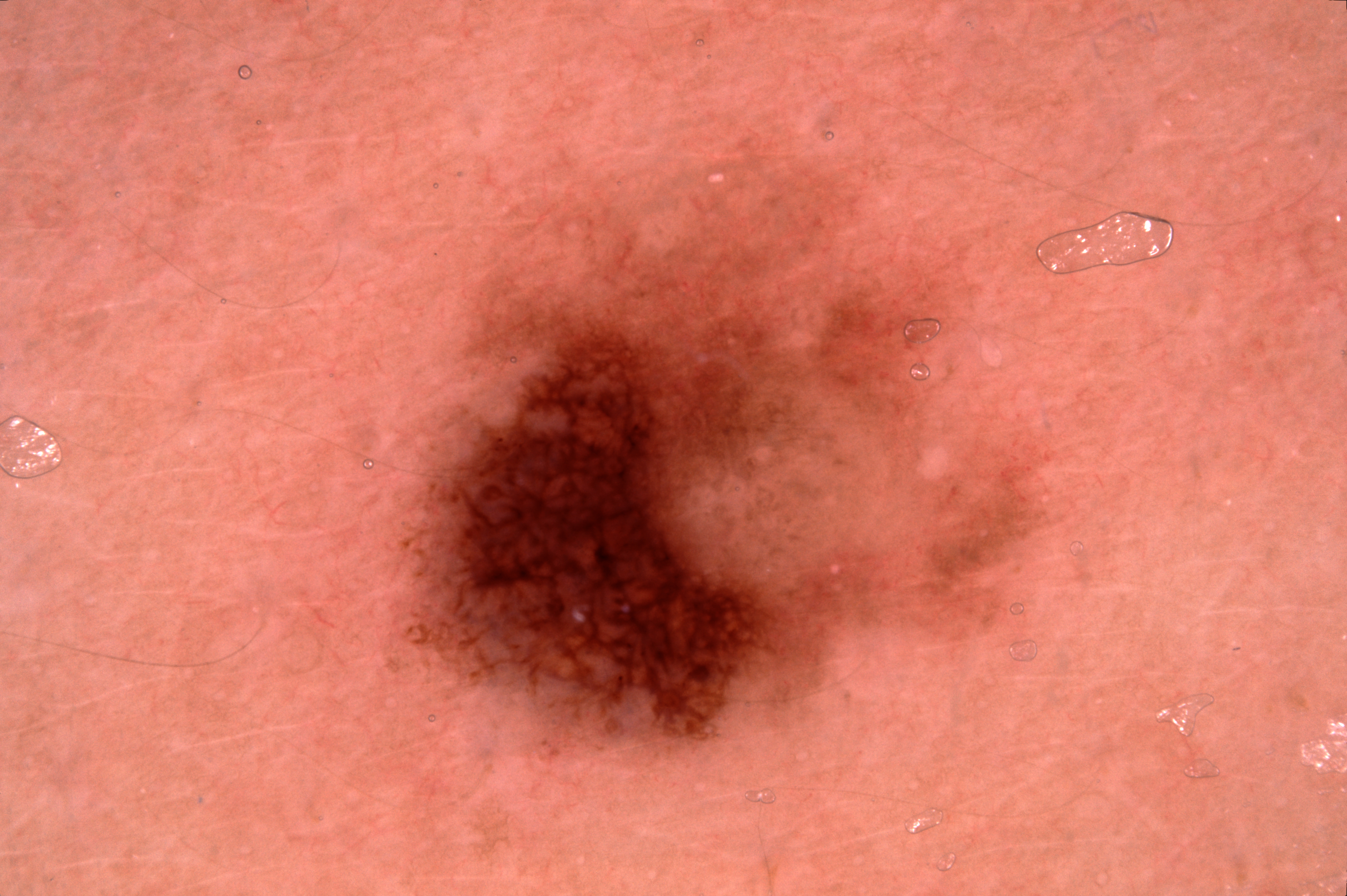Q: What is the imaging modality?
A: dermoscopy
Q: Where is the lesion in the image?
A: <box>397, 159, 1061, 761</box>
Q: Which dermoscopic features were noted?
A: pigment network; absent: negative network, milia-like cysts, and streaks
Q: What did the assessment conclude?
A: a melanocytic nevus, a benign lesion